The subject is a female roughly 55 years of age; a dermoscopic view of a skin lesion:
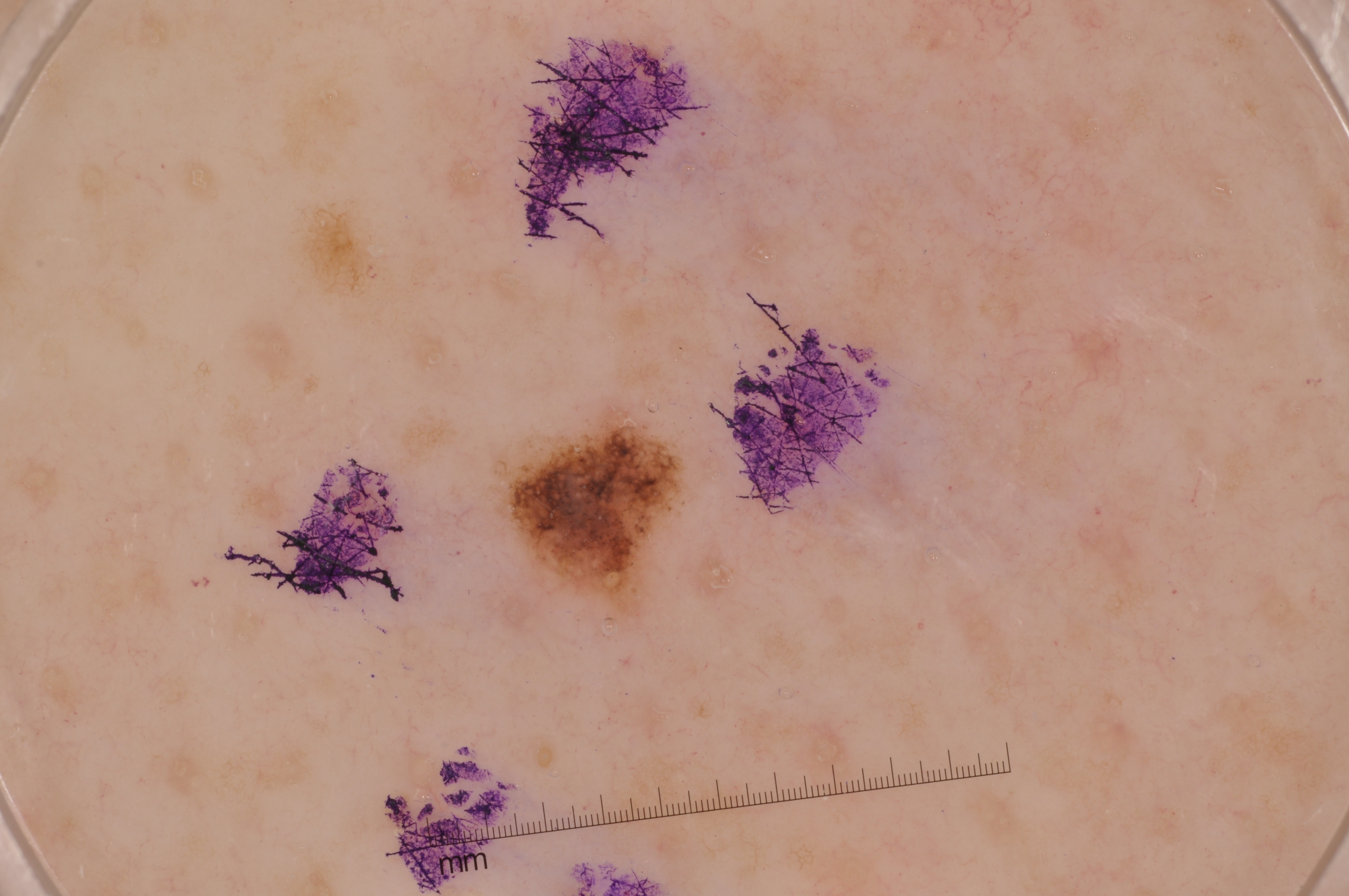Dermoscopically, the lesion shows pigment network and milia-like cysts; no streaks or negative network.
The lesion is bounded by x1=506, y1=427, x2=674, y2=595.
The lesion was assessed as a melanocytic nevus.